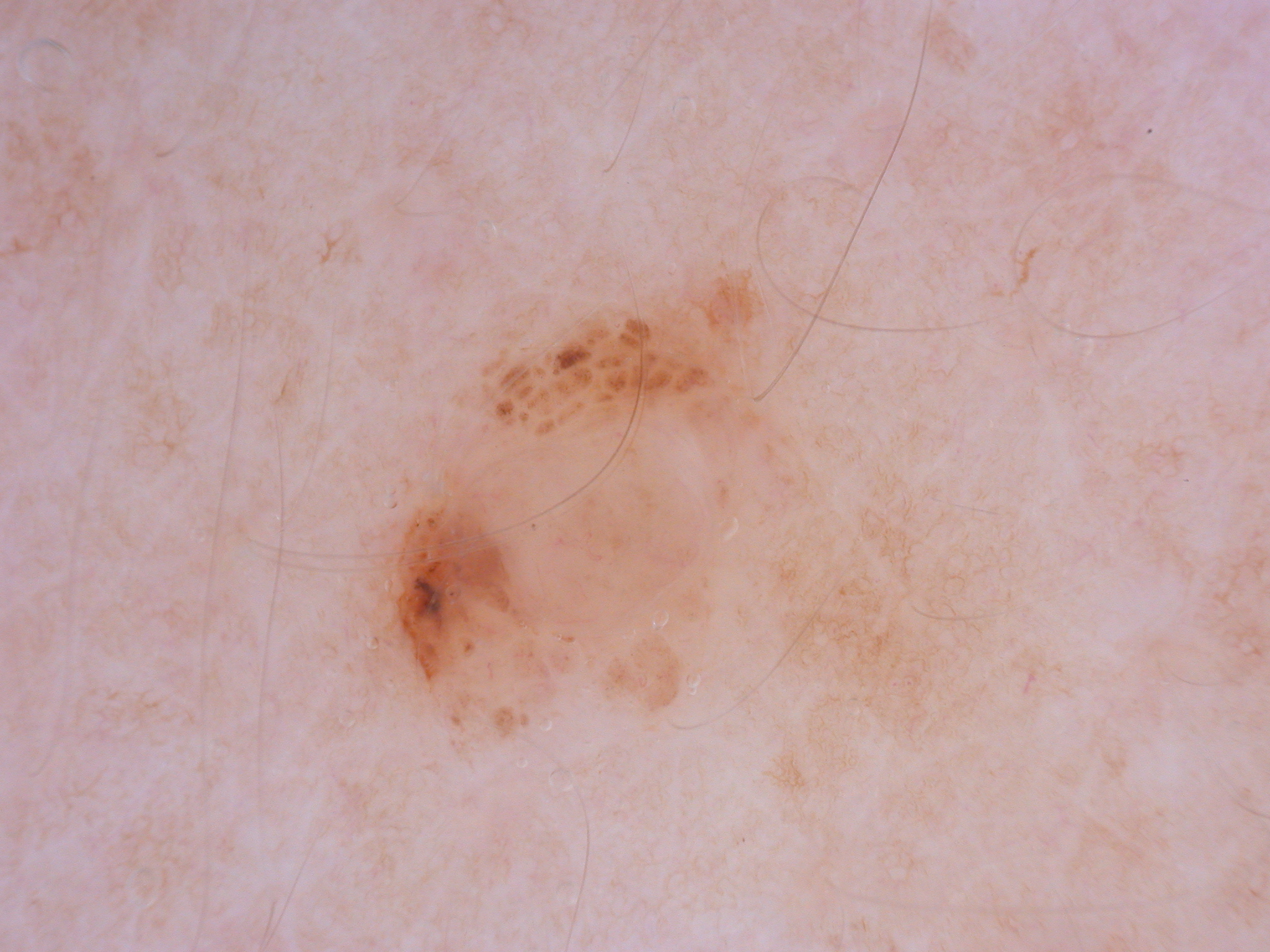This is a dermoscopic photograph of a skin lesion. Dermoscopic assessment notes globules. The lesion covers approximately 11% of the dermoscopic field. With coordinates (x1, y1, x2, y2), the lesion occupies the region [349,260,822,736]. Consistent with a melanocytic nevus, a benign skin lesion.